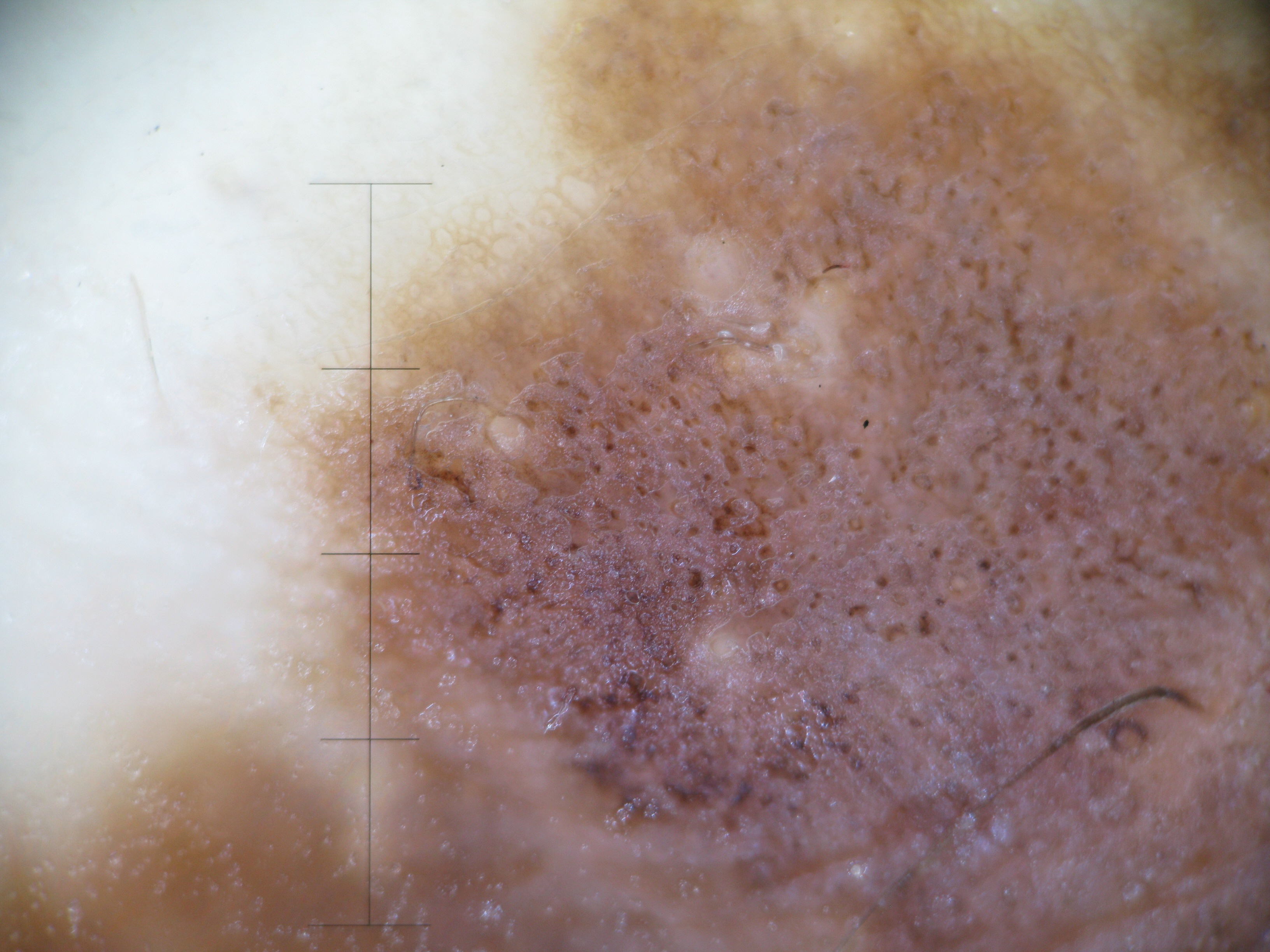  image: dermoscopy
  diagnosis:
    name: congenital compound nevus
    code: ccb
    malignancy: benign
    super_class: melanocytic
    confirmation: expert consensus